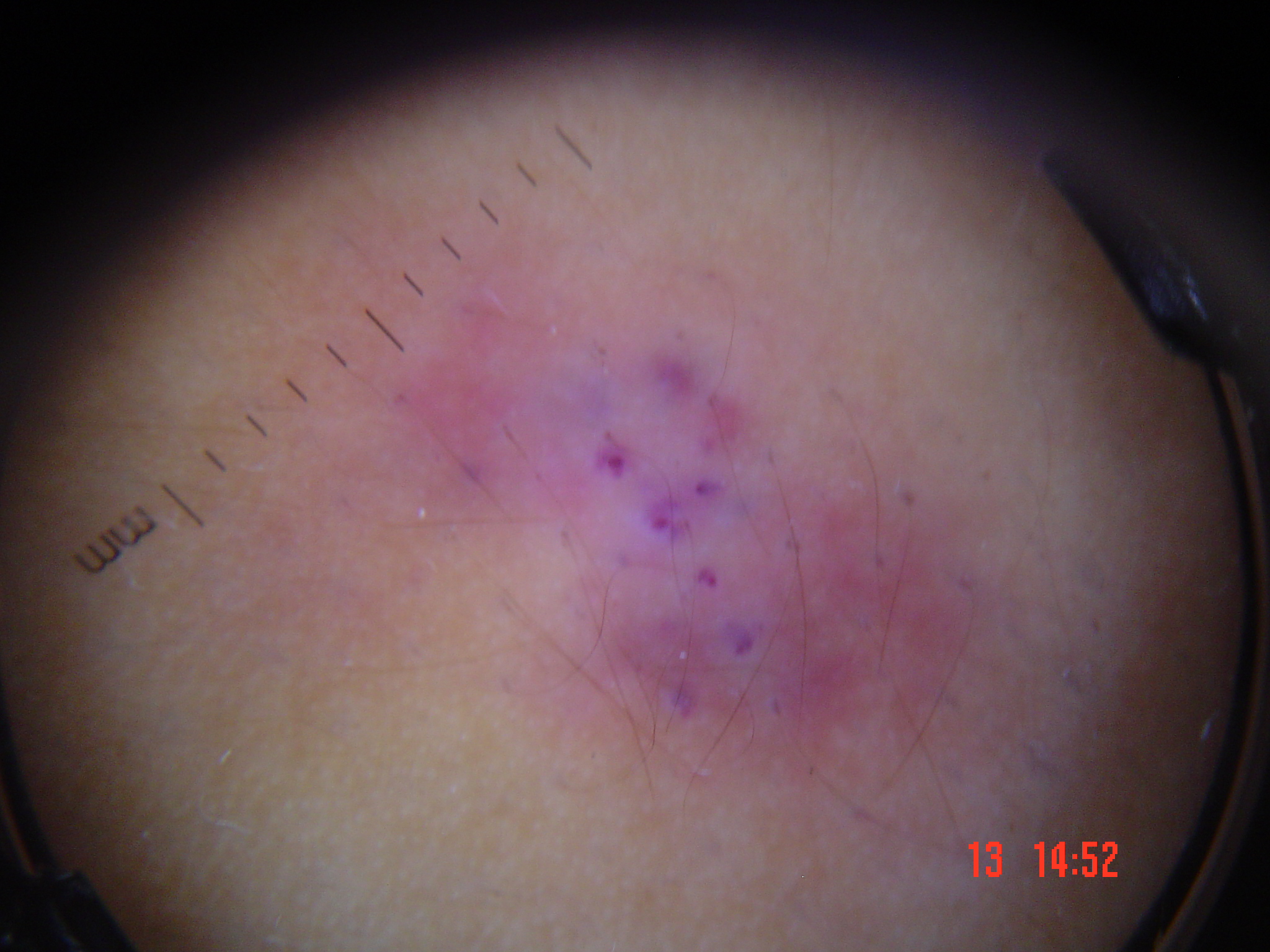A dermoscopic photograph of a skin lesion. The architecture is that of a vascular lesion. Labeled as a benign lesion — an angiokeratoma.